A female patient 75 years of age. Imaged for a research study, with no referral diagnosis recorded. A dermoscopic image of a skin lesion: 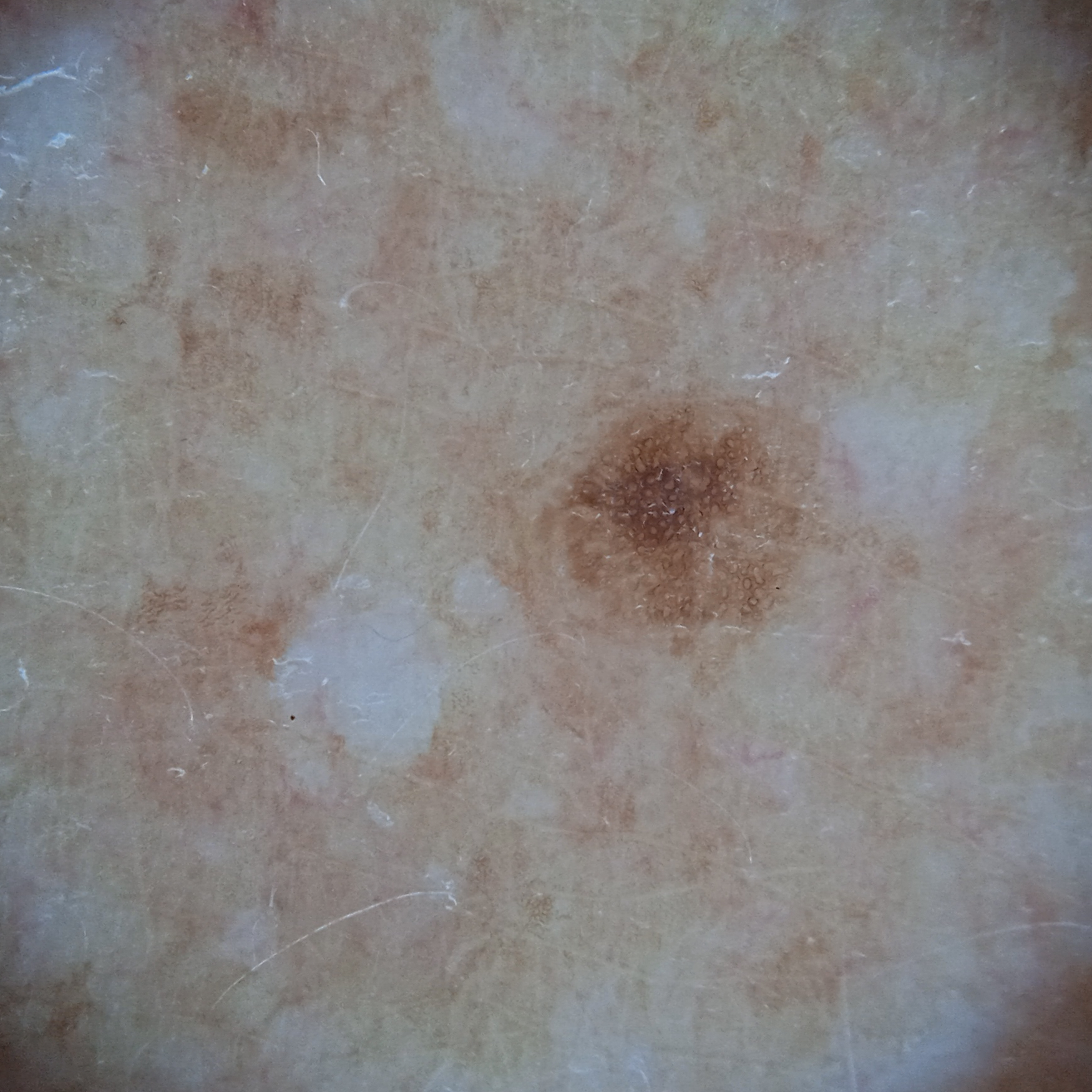The lesion involves the back.
The lesion is about 2.7 mm across.
The diagnostic impression was a melanocytic nevus.